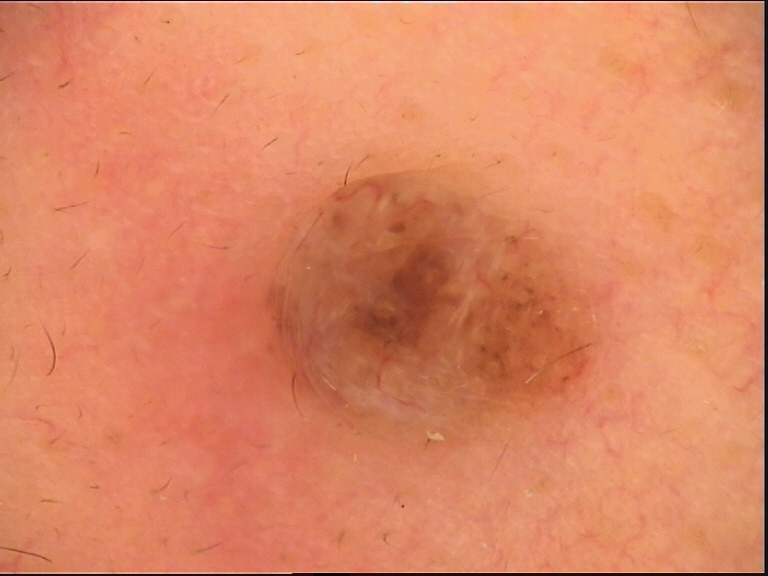Classified as a dermal nevus.